The photograph is a close-up of the affected area, the lesion involves the leg and sole of the foot — 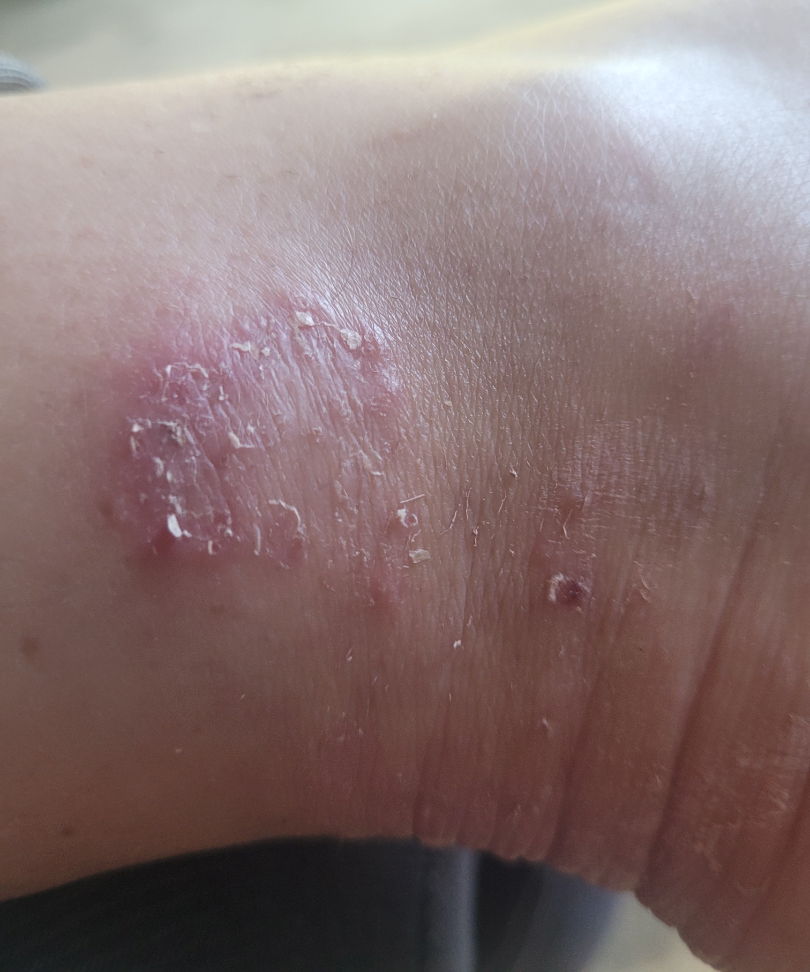The reviewing dermatologist's impression was: favoring Tinea.